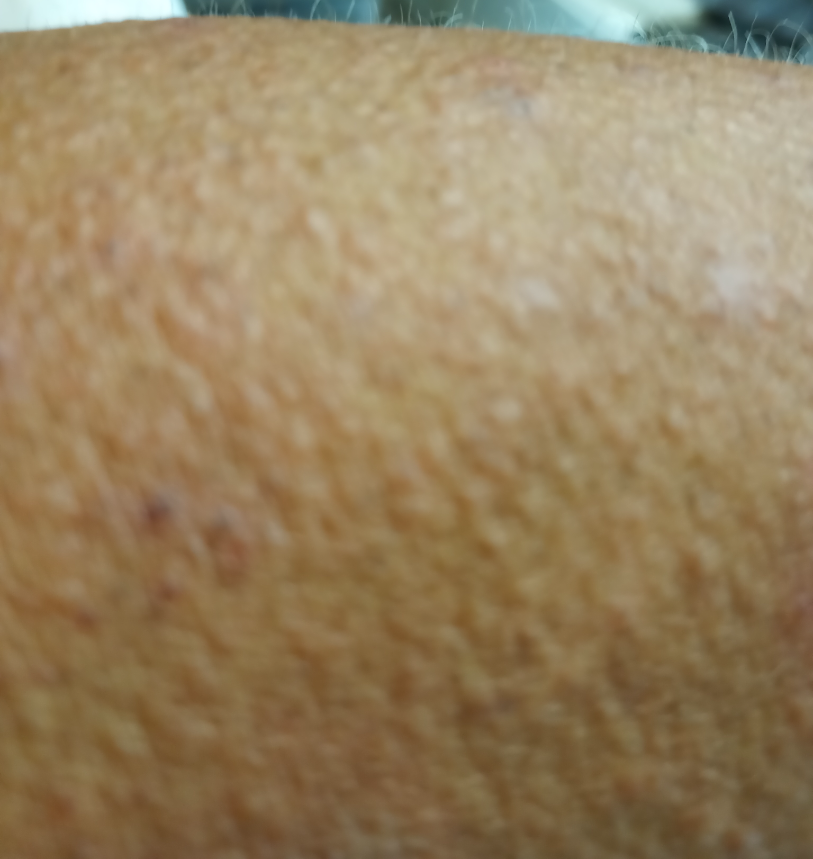shot type: close-up
lesion texture: raised or bumpy
patient describes the issue as: a rash
subject: male, age 40–49
reported symptoms: bothersome appearance and itching
onset: one to four weeks
skin tone: Fitzpatrick skin type IV; non-clinician graders estimated 5 on the Monk skin tone scale
affected area: front of the torso, arm and leg
constitutional symptoms: none reported